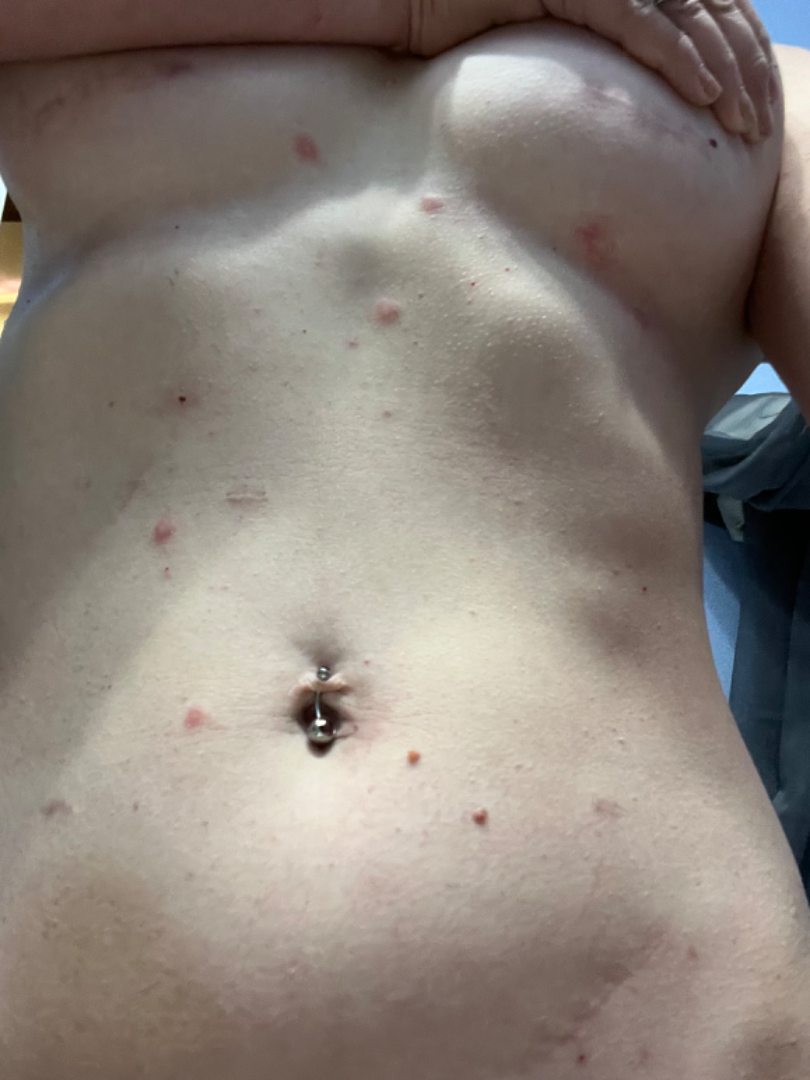The patient described the issue as a rash. The contributor notes the condition has been present for less than one week. The lesion is described as fluid-filled and raised or bumpy. The front of the torso is involved. A close-up photograph. The contributor is a female aged 30–39. Three dermatologists independently reviewed the case: the leading consideration is Insect Bite; also raised was Folliculitis; also consider Lymphomatoid papulosis.